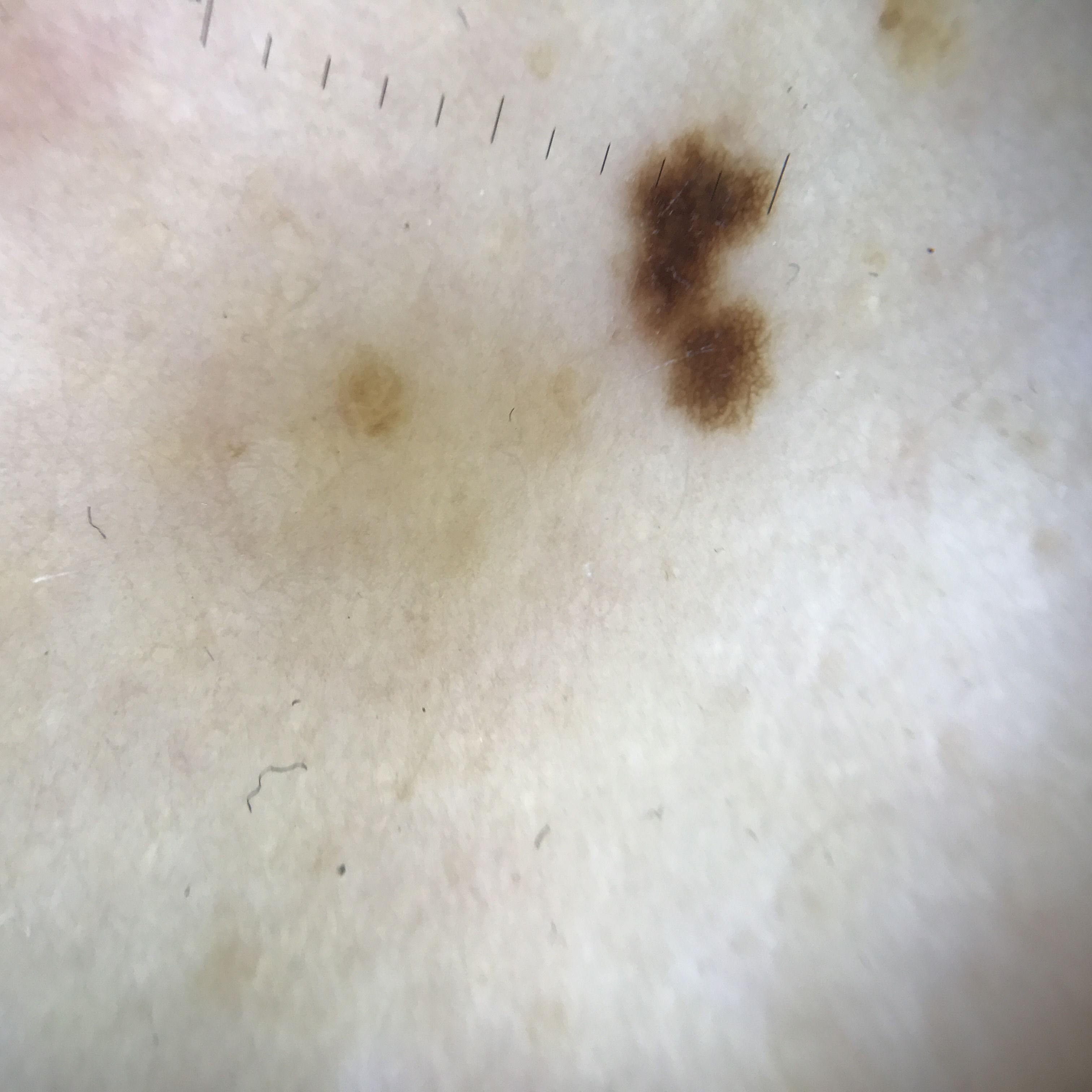Dermoscopy of a skin lesion.
Labeled as a benign lesion — a dysplastic junctional nevus.